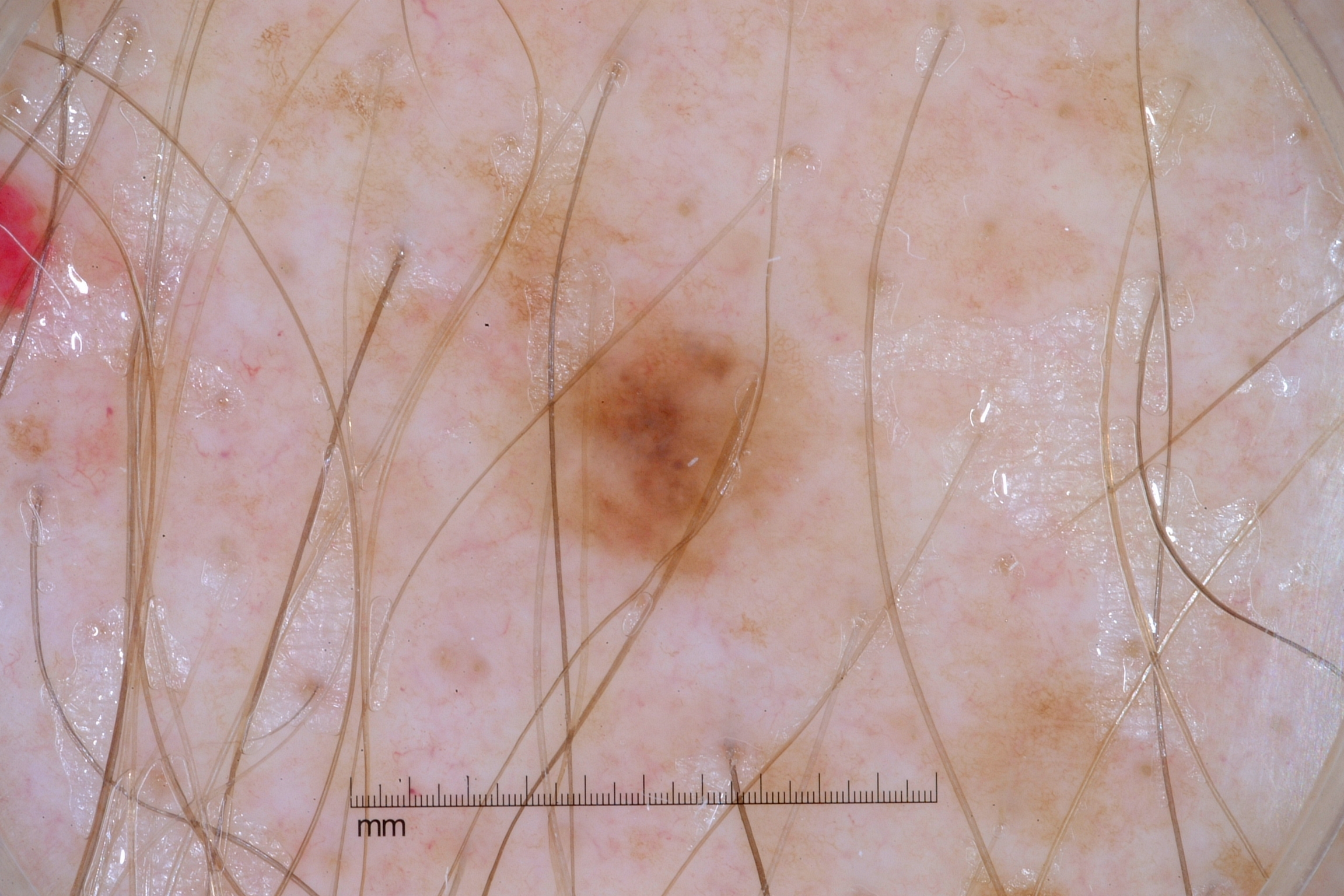modality — dermoscopy of a skin lesion
subject — male, roughly 60 years of age
location — box(488, 274, 838, 605)
dermoscopic pattern — milia-like cysts and pigment network
size — small
diagnosis — a melanocytic nevus, a benign lesion